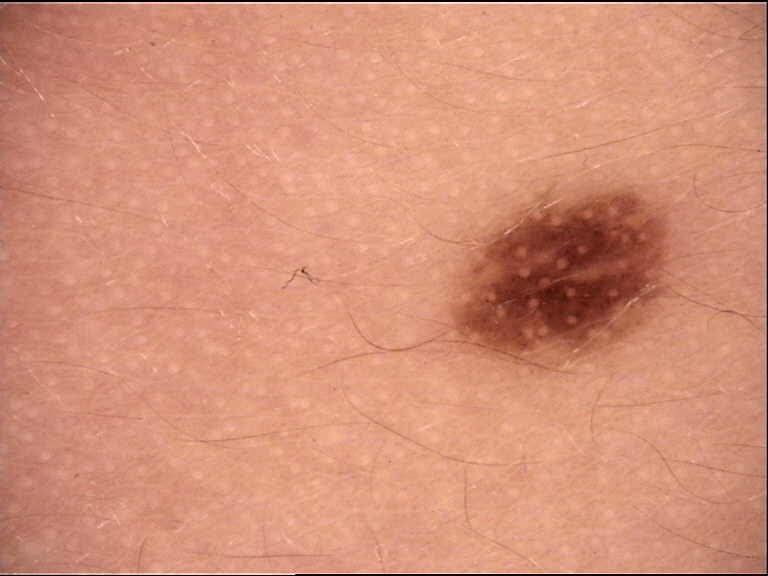A dermoscopic close-up of a skin lesion.
This is a banal lesion.
Consistent with a congenital junctional nevus.